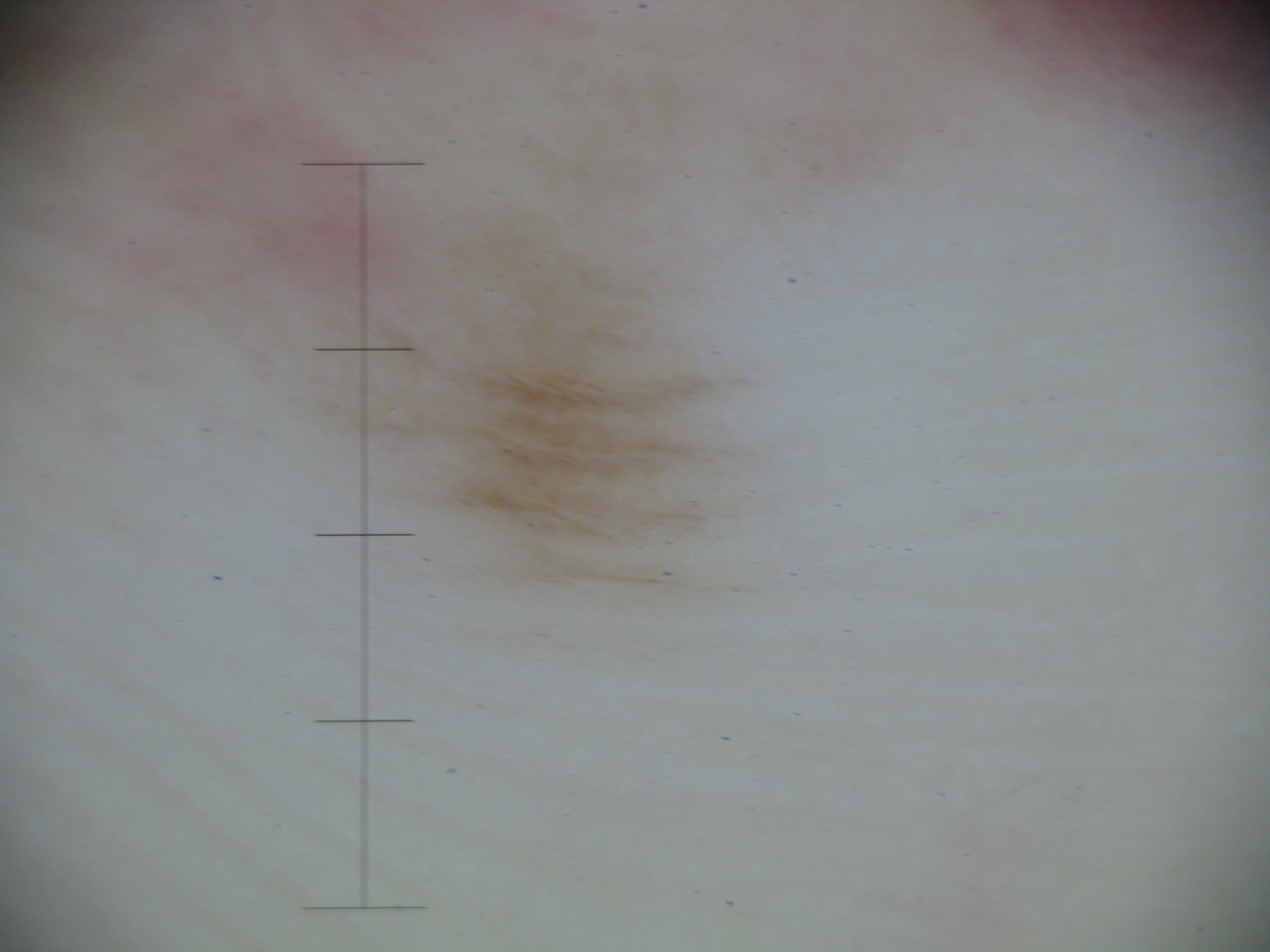A dermoscopy image of a single skin lesion. Labeled as a banal lesion — an acral junctional nevus.